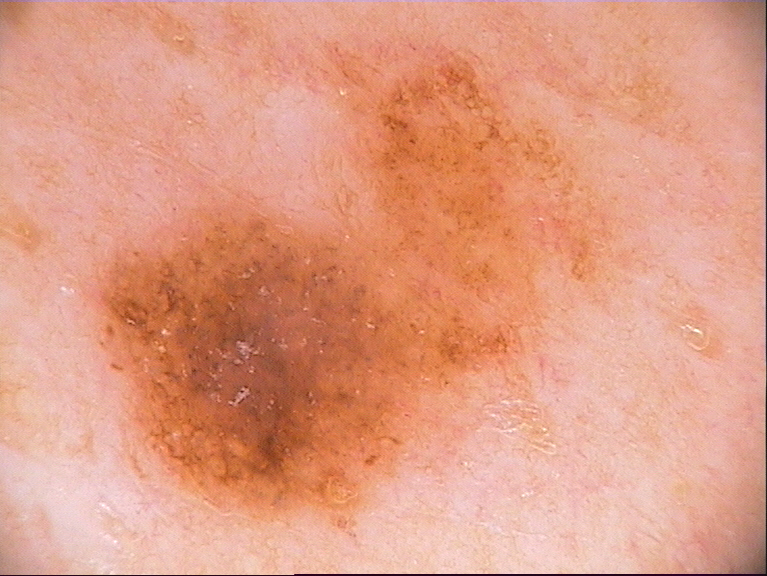Case summary:
• subject — male, approximately 50 years of age
• imaging — dermoscopy
• lesion bbox — bbox=[87, 47, 622, 545]
• extent — ~39% of the field
• features — pigment network and globules
• diagnostic label — a melanocytic nevus